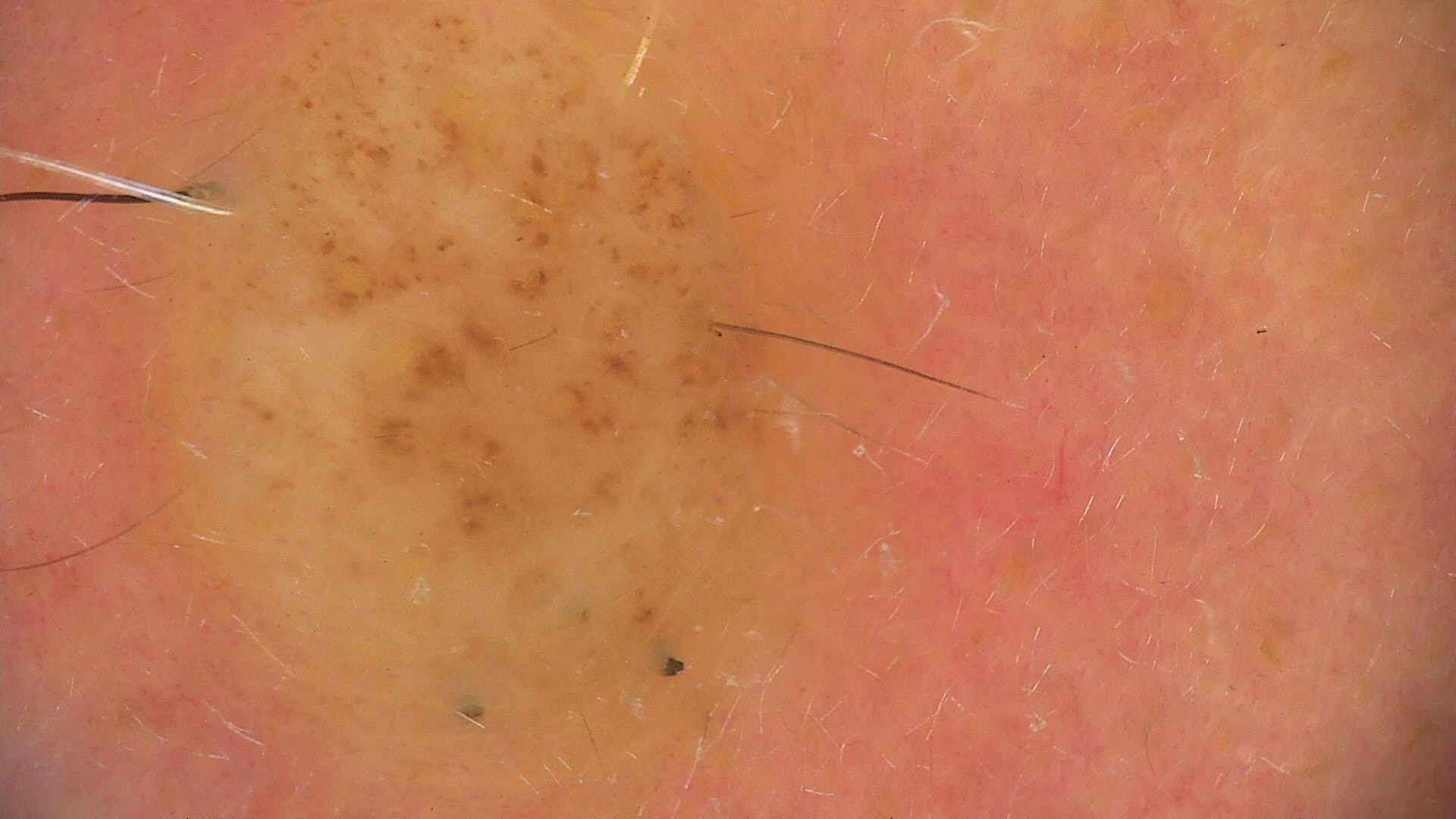  image: dermoscopy
  lesion_type:
    main_class: banal
    pattern: dermal
  diagnosis:
    name: dermal nevus
    code: db
    malignancy: benign
    super_class: melanocytic
    confirmation: expert consensus